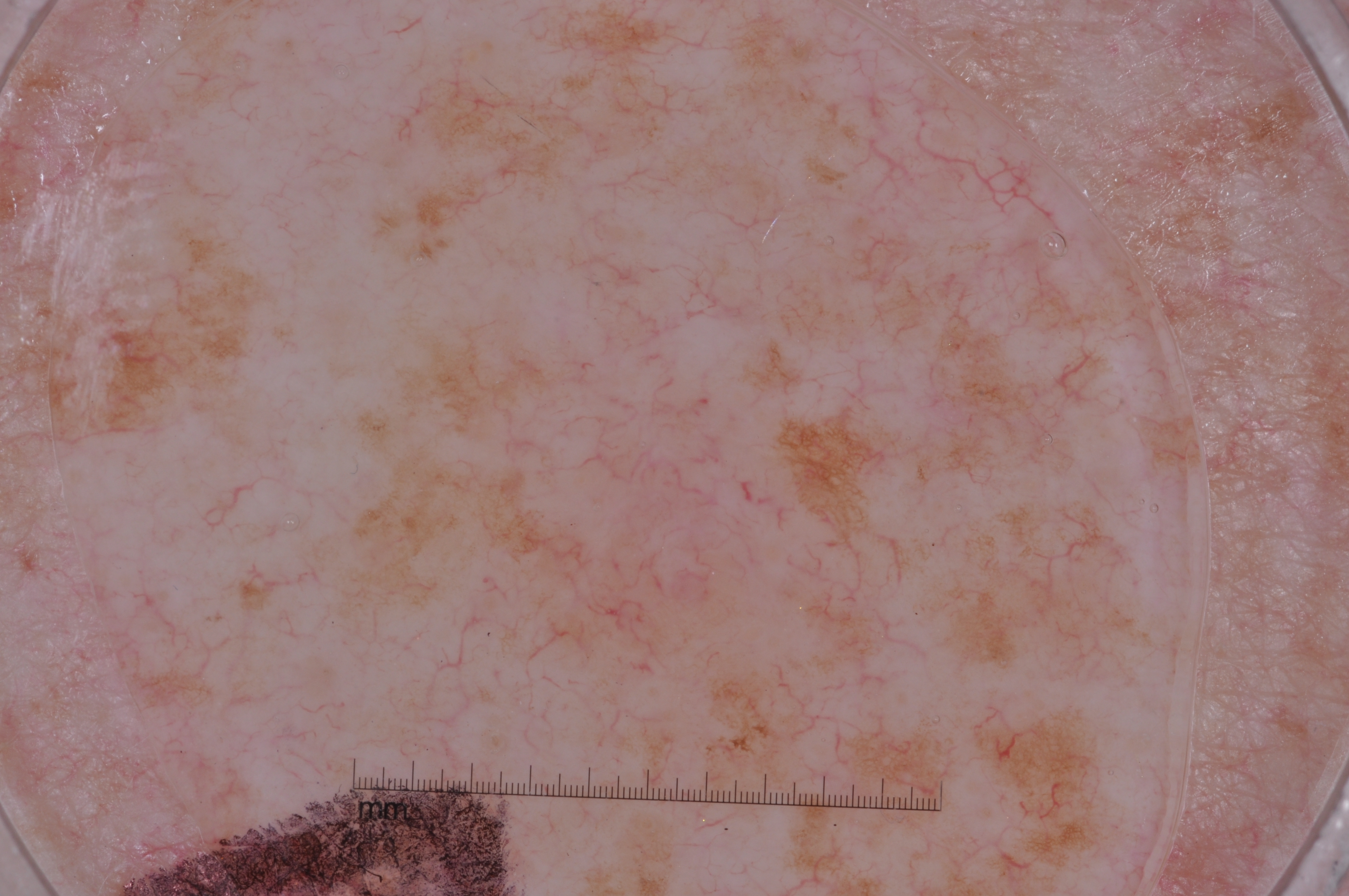{
  "image": {
    "modality": "dermoscopy"
  },
  "patient": {
    "sex": "male",
    "age_approx": 60
  },
  "lesion_location": {
    "bbox_xyxy": [
      296,
      228,
      1010,
      855
    ]
  },
  "dermoscopic_features": {
    "present": [
      "pigment network"
    ],
    "absent": [
      "streaks",
      "milia-like cysts",
      "negative network"
    ]
  },
  "lesion_extent": "moderate",
  "diagnosis": {
    "name": "melanocytic nevus",
    "malignancy": "benign",
    "lineage": "melanocytic",
    "provenance": "clinical"
  }
}